A skin lesion imaged with a dermatoscope.
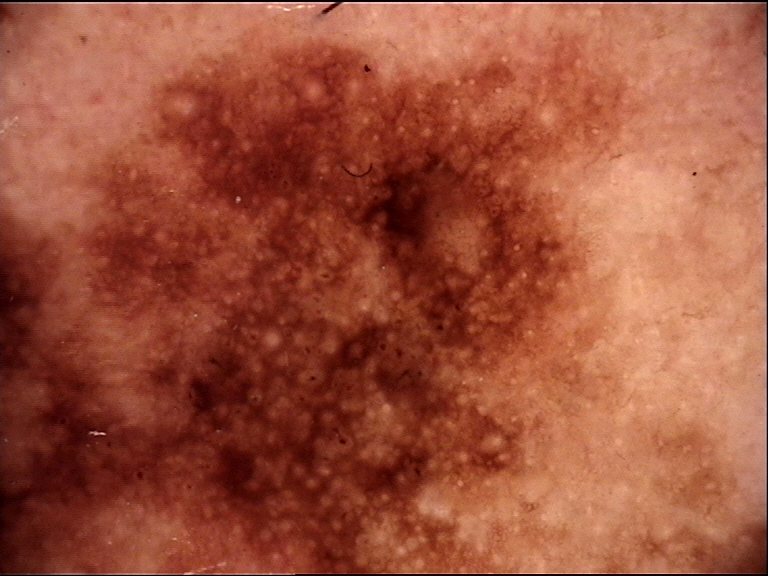Histopathology confirmed a lentigo maligna.